An image taken at an angle. FST III; lay graders estimated Monk Skin Tone 5 (US pool) or 3 (India pool) — 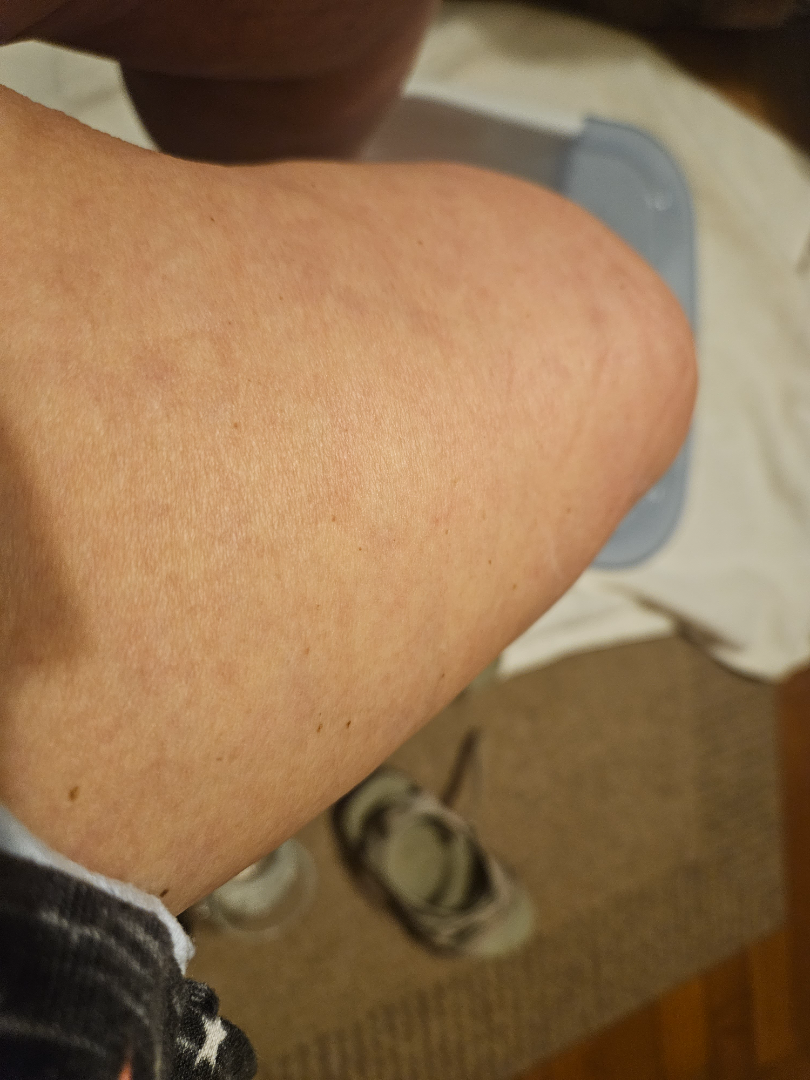{
  "assessment": "unable to determine"
}